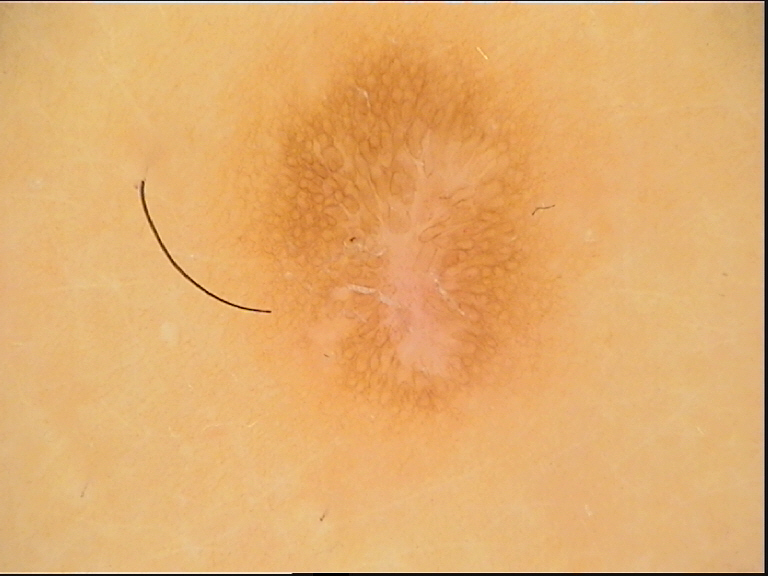image type: dermatoscopy | subtype: fibro-histiocytic | assessment: dermatofibroma (expert consensus).